The patient considered this a rash · this is a close-up image · FST II · the lesion is described as rough or flaky and raised or bumpy · symptoms reported: itching, darkening, enlargement and burning · located on the front of the torso:
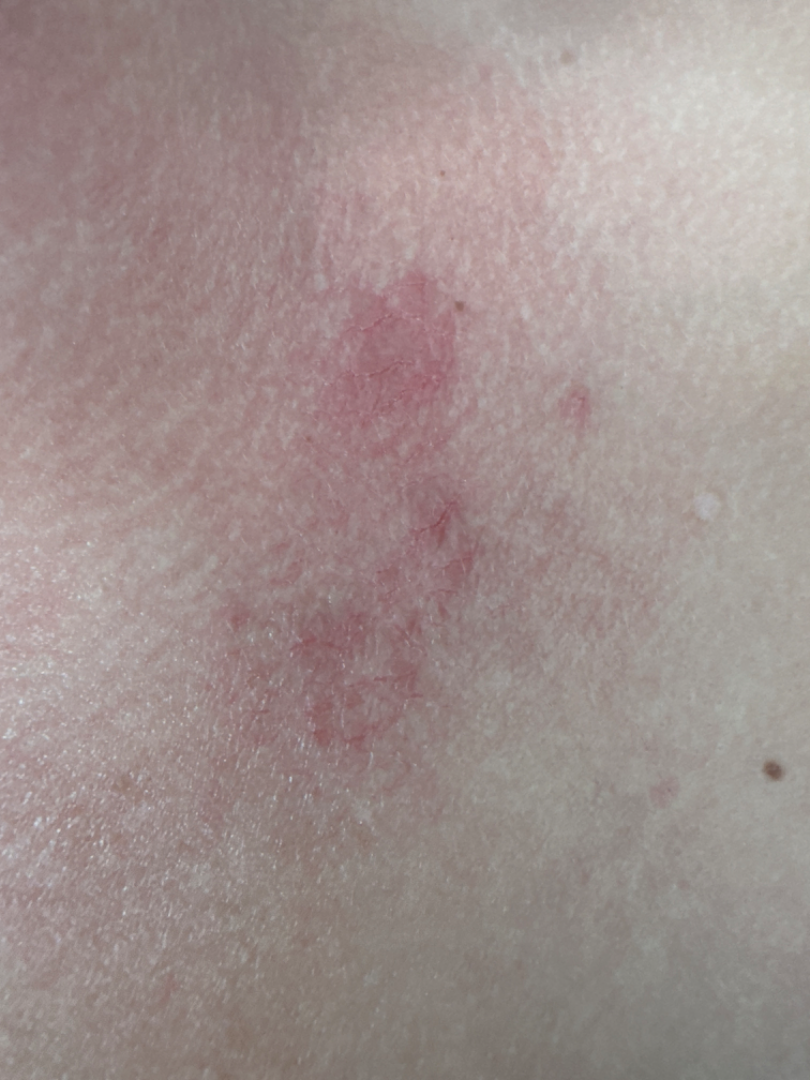Findings:
* assessment · could not be assessed